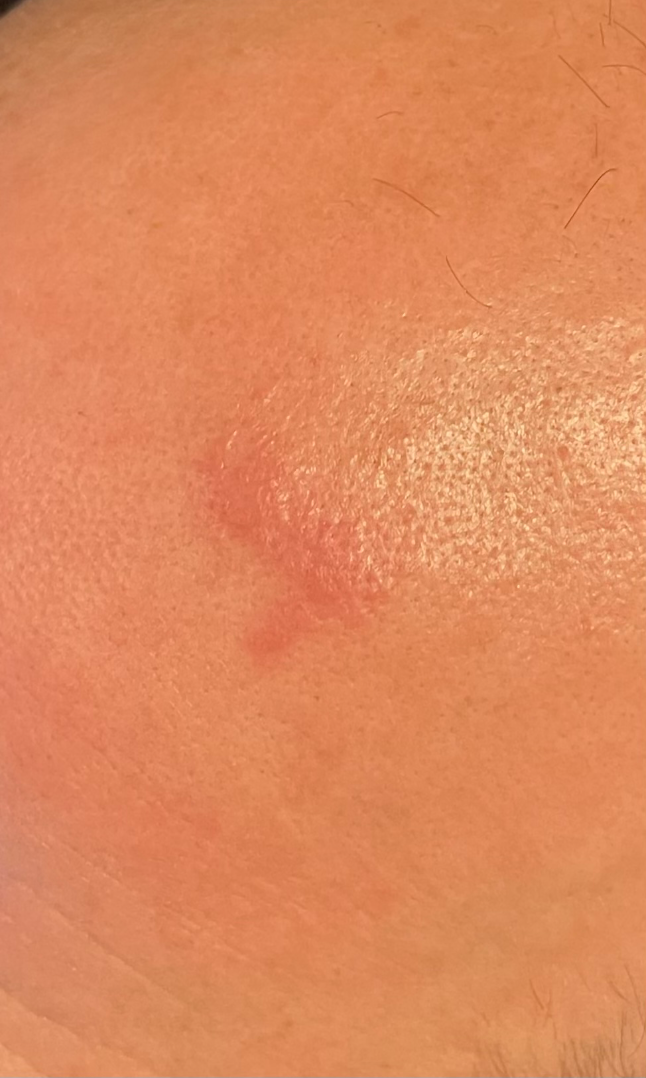Q: What was the assessment?
A: not assessable
Q: Duration?
A: less than one week
Q: Anatomic location?
A: head or neck
Q: What is the framing?
A: close-up
Q: Texture?
A: raised or bumpy and fluid-filled